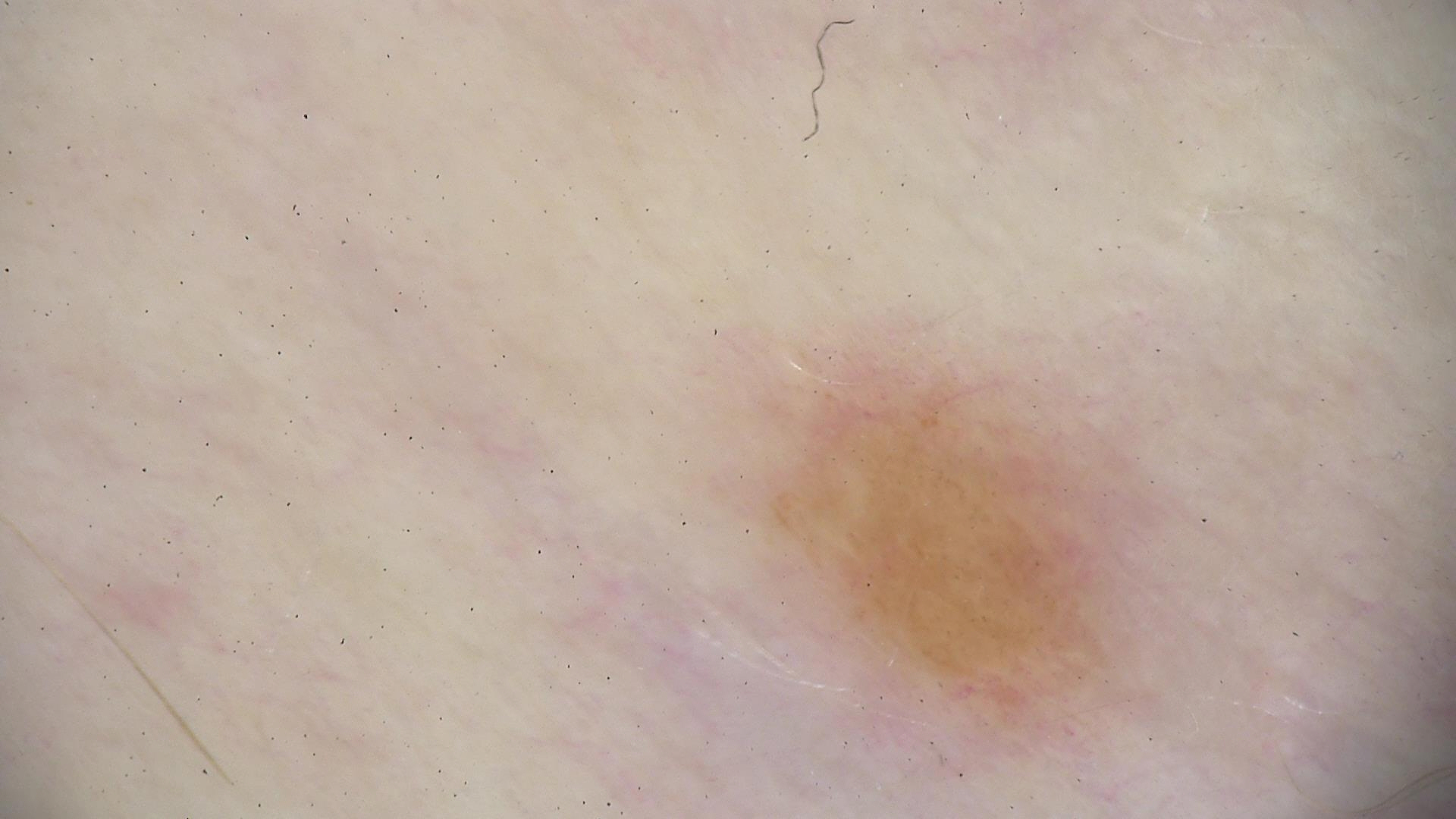  image: dermatoscopy
  lesion_type:
    main_class: banal
    pattern: junctional
  diagnosis:
    name: junctional nevus
    code: jb
    malignancy: benign
    super_class: melanocytic
    confirmation: expert consensus